Dermoscopy of a skin lesion.
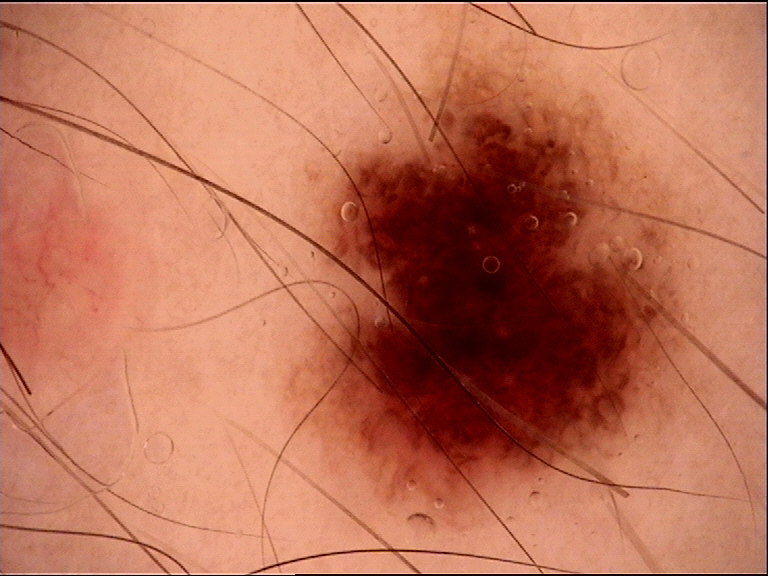label: dysplastic junctional nevus (expert consensus).